The patient indicates itching. This image was taken at an angle. Self-categorized by the patient as a rash. The affected area is the arm and leg. Reported duration is less than one week. The subject is a male aged 30–39. Texture is reported as raised or bumpy and fluid-filled: 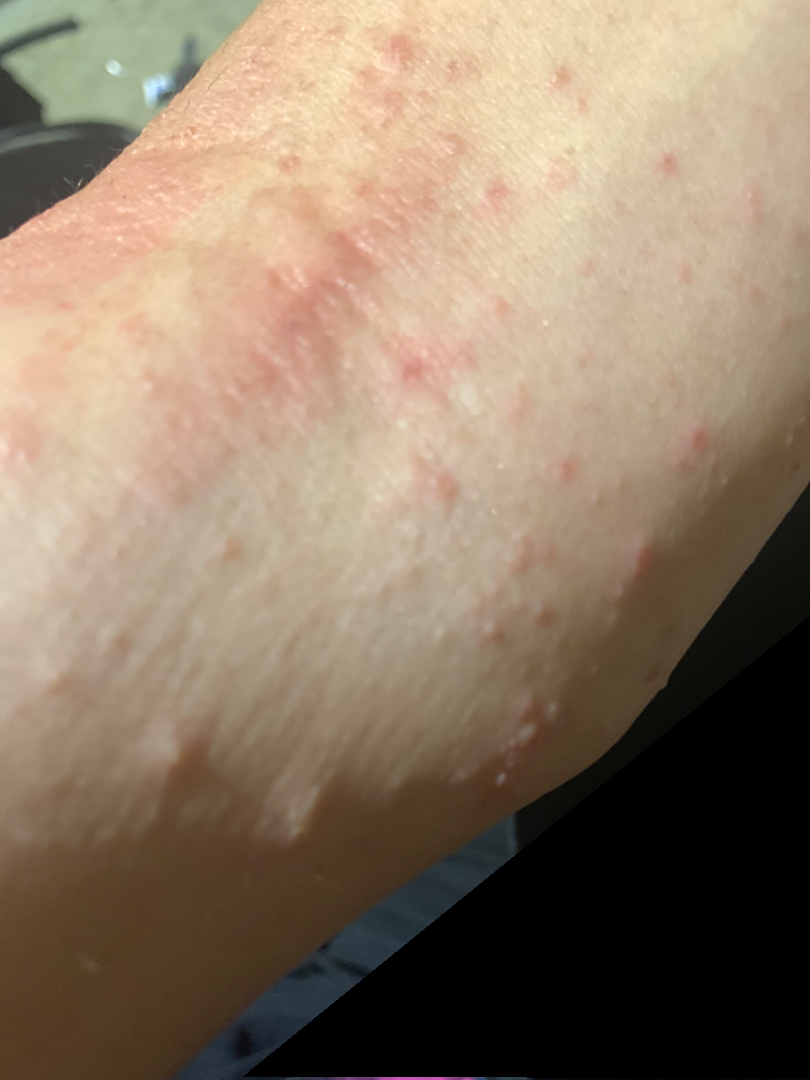Review:
The reviewing dermatologists' impression was: most likely Eczema; an alternative is Allergic Contact Dermatitis; less probable is Molluscum Contagiosum; lower on the differential is Hypersensitivity; less likely is Irritant Contact Dermatitis.